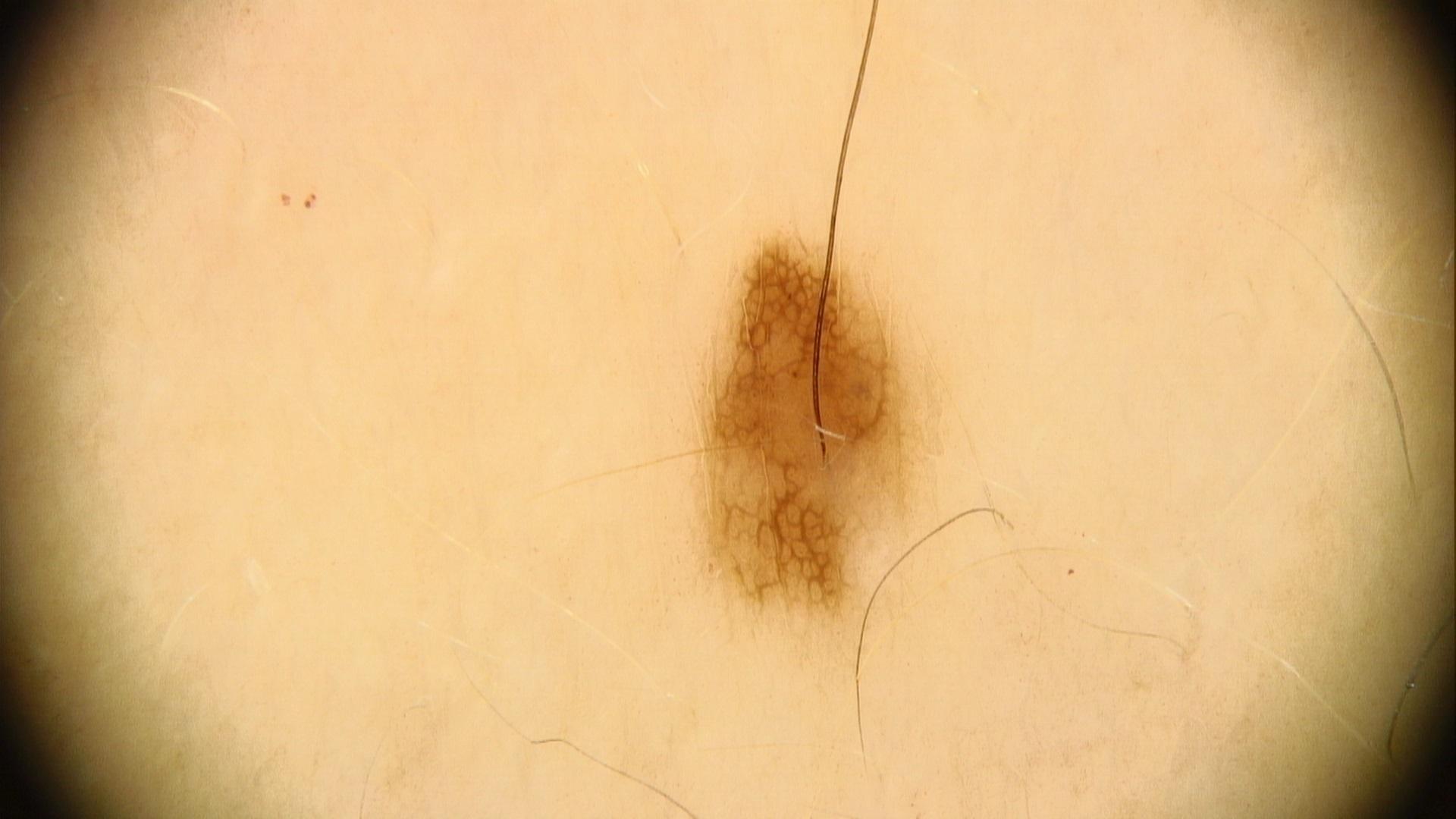Case summary:
Dermoscopy of a skin lesion. A female patient aged approximately 55. The lesion involves a lower extremity.
Conclusion:
The clinical assessment was a nevus.